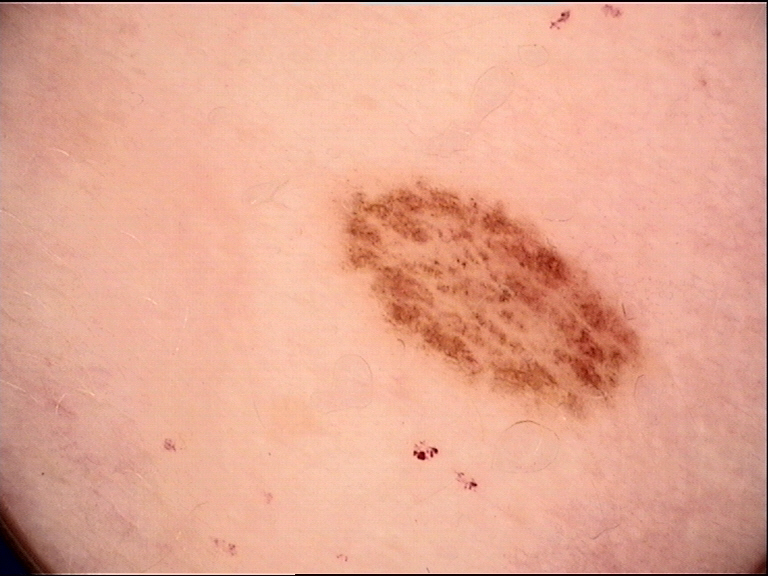diagnosis:
  name: dysplastic junctional nevus
  code: jd
  malignancy: benign
  super_class: melanocytic
  confirmation: expert consensus